A dermatoscopic image of a skin lesion · a male subject, aged approximately 70:
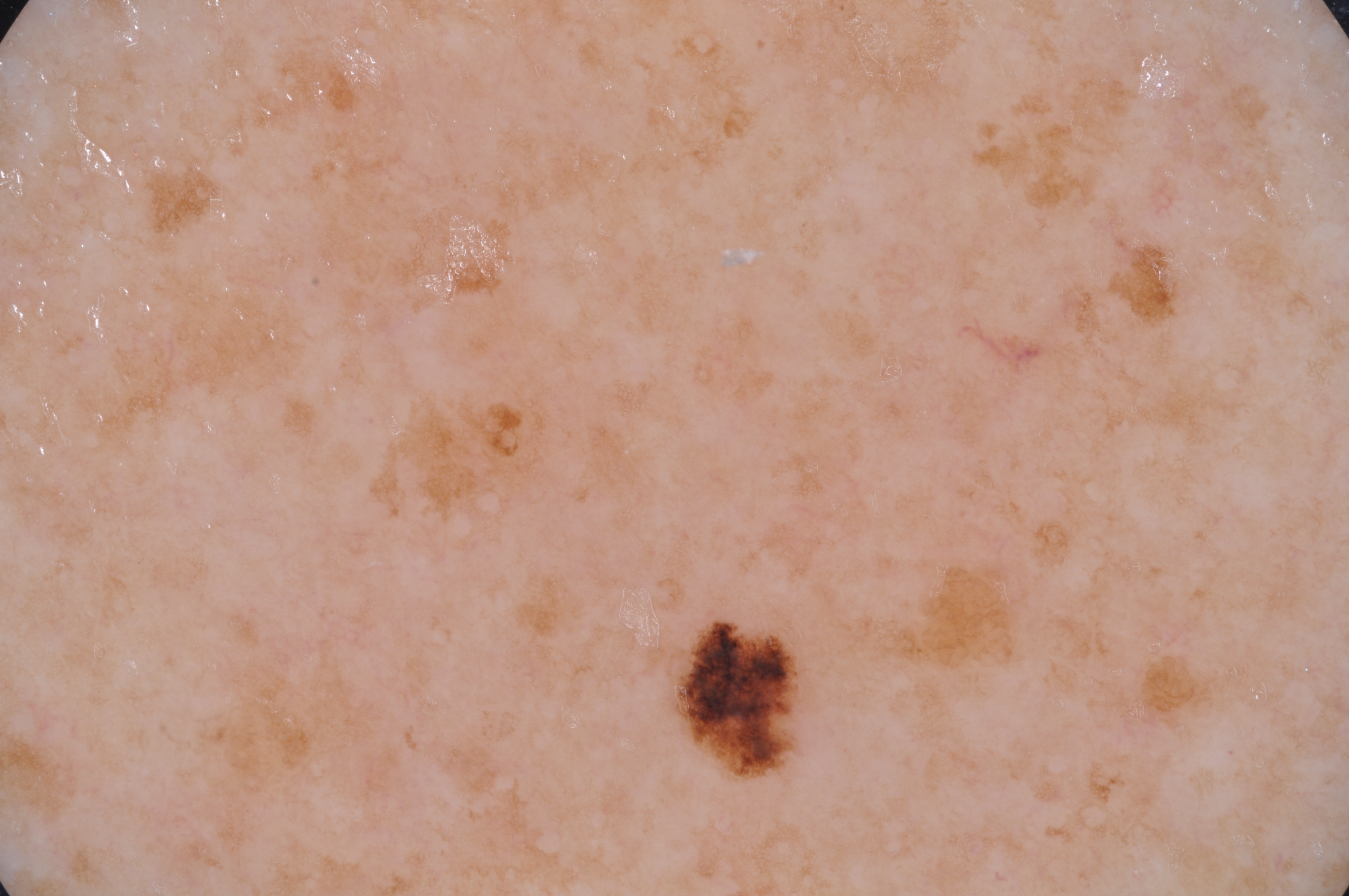Dermoscopically, the lesion shows pigment network. In (x1, y1, x2, y2) order, the lesion's extent is bbox(671, 619, 799, 779). Diagnosed as a melanocytic nevus, a benign skin lesion.